A female patient aged 58 · acquired for a research image collection, with no referral diagnosis · the patient says their skin tans without first burning · the patient reports a family history of skin cancer, a personal history of cancer, and a personal history of skin cancer.
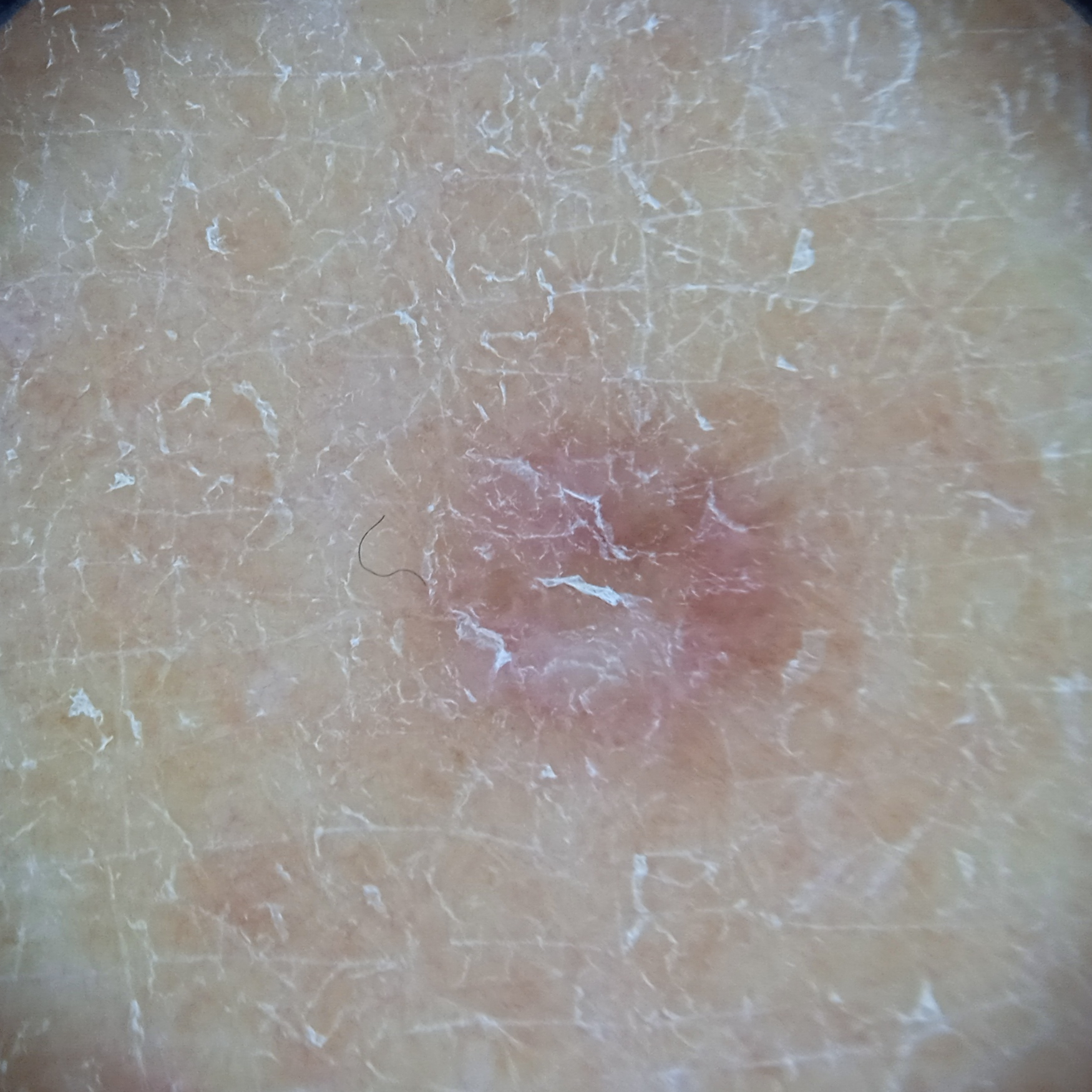{
  "lesion_size": {
    "diameter_mm": 5.2
  },
  "diagnosis": {
    "name": "dermatofibroma",
    "malignancy": "benign"
  }
}